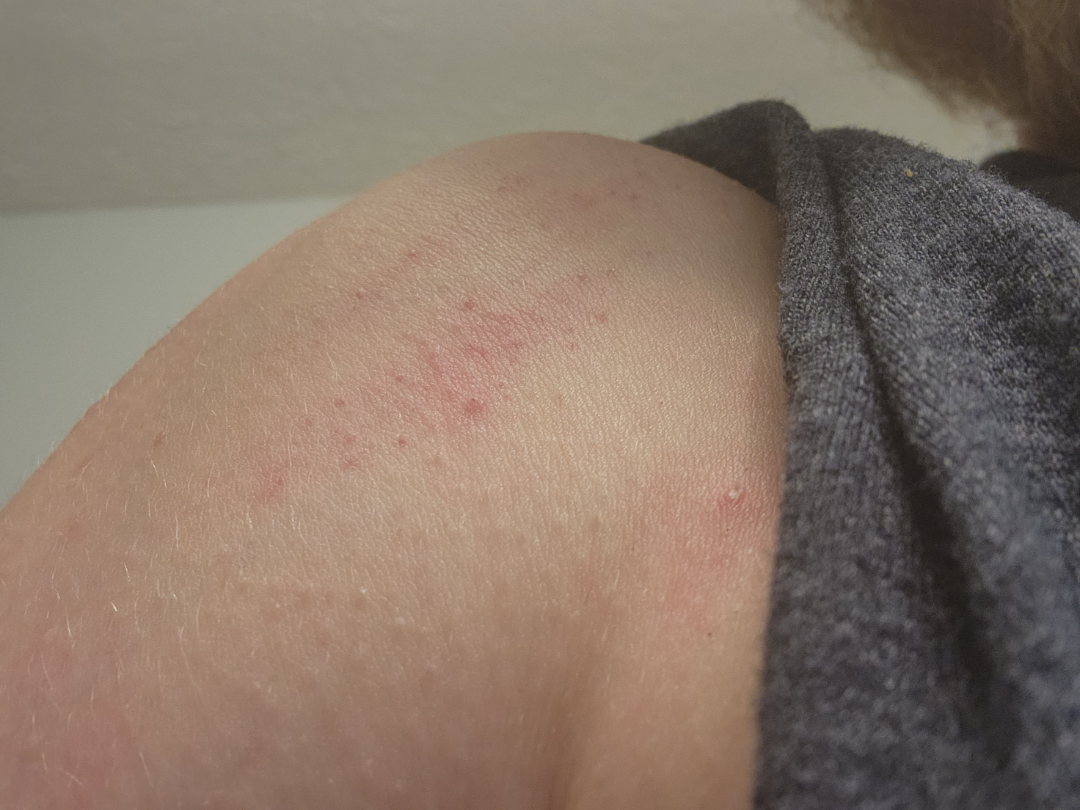The photograph was taken at an angle. Folliculitis (most likely); Keratosis pilaris (possible); Irritant Contact Dermatitis (possible).